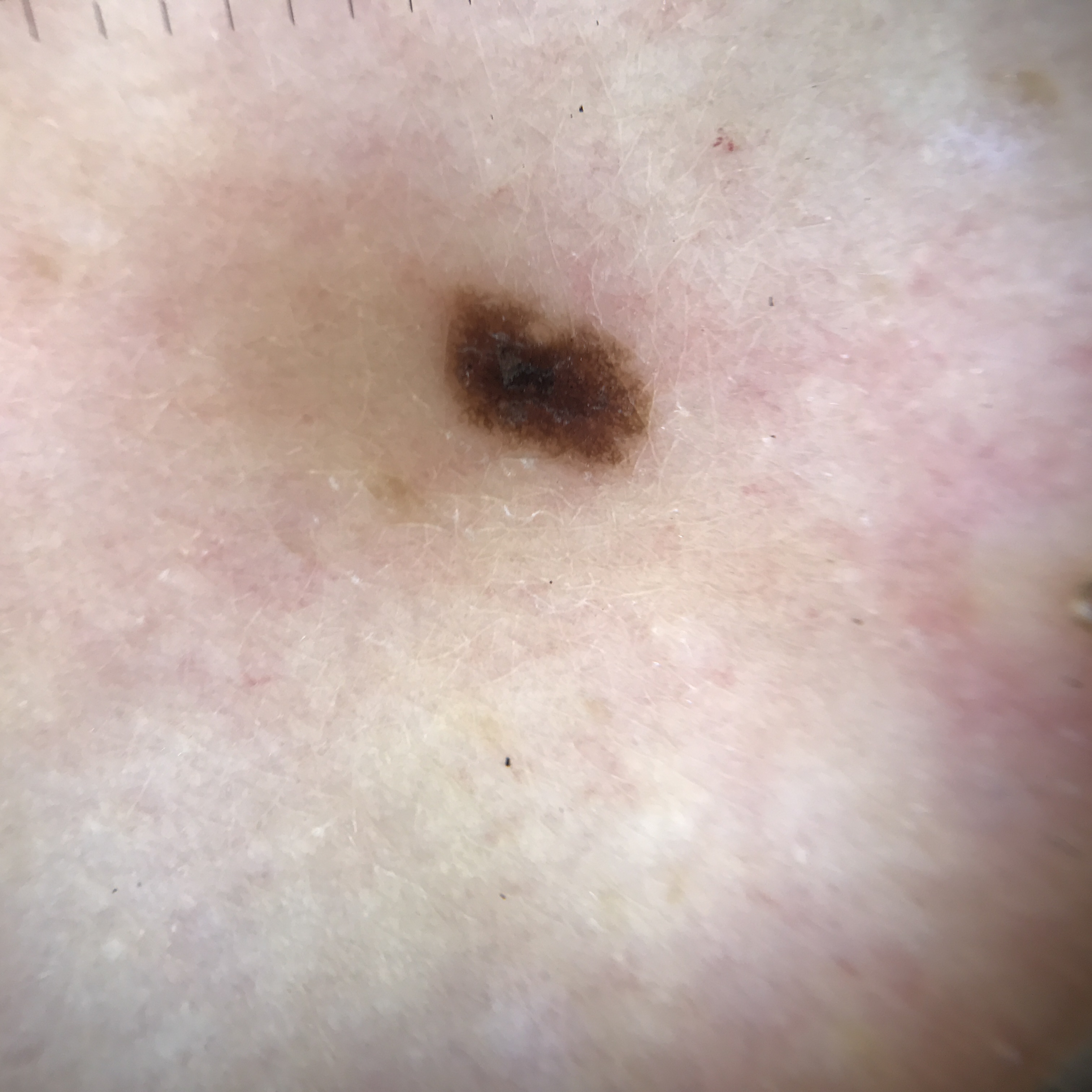A dermoscopic photograph of a skin lesion.
Labeled as a benign lesion — a dysplastic junctional nevus.